A dermoscopic image of a skin lesion.
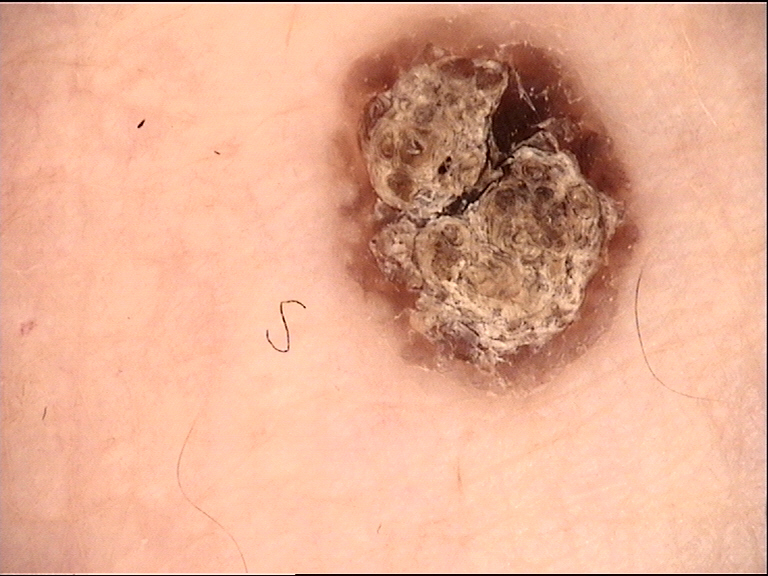label — seborrheic keratosis (expert consensus).